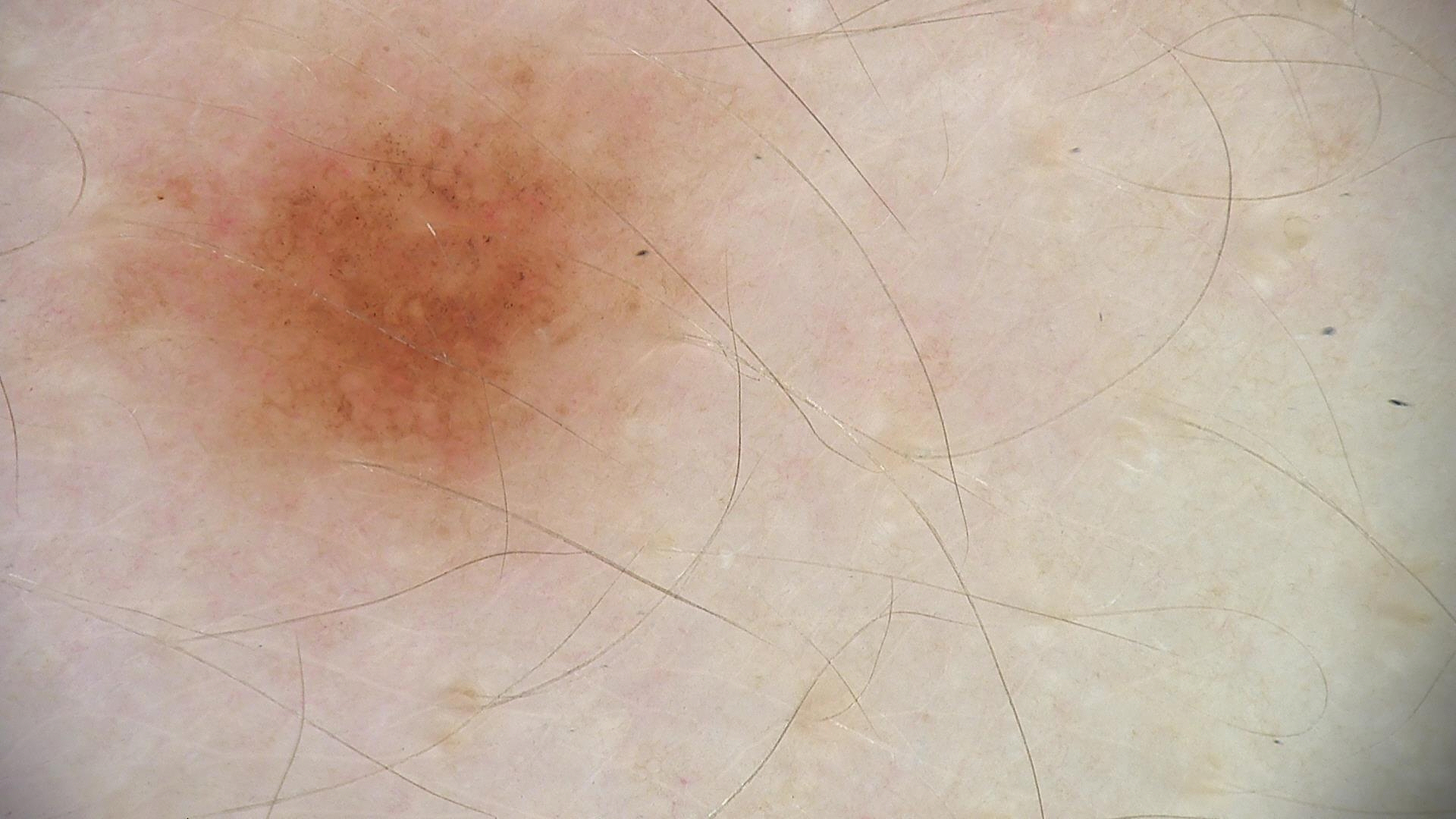A dermoscopic close-up of a skin lesion. This is a banal lesion. The diagnostic label was a compound nevus.